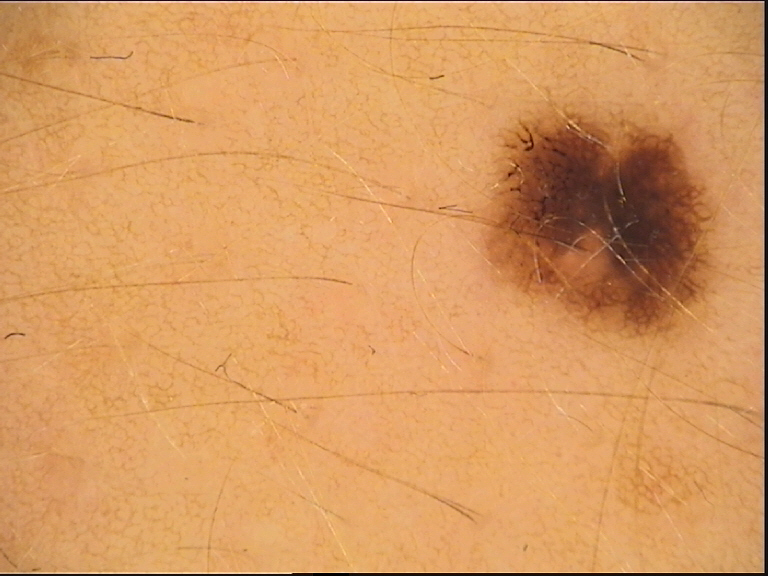A dermoscopy image of a single skin lesion. Labeled as a benign lesion — a dysplastic junctional nevus.